A dermoscopy image of a single skin lesion — 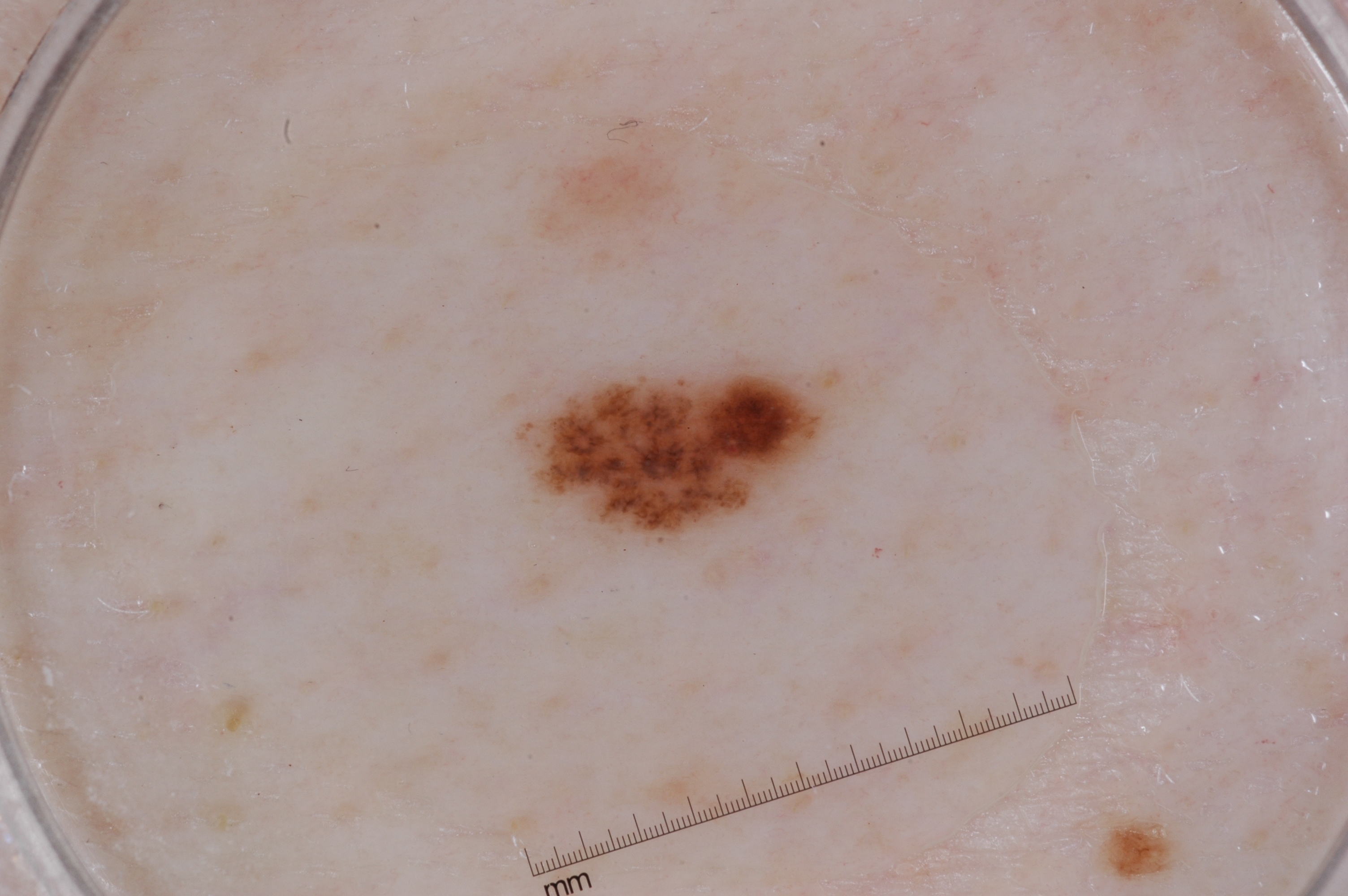The lesion is located at [515, 359, 832, 545]. On dermoscopy, the lesion shows no milia-like cysts, negative network, pigment network, or streaks. The lesion takes up about 3% of the image. Diagnosed as a melanocytic nevus.